Close-up view — 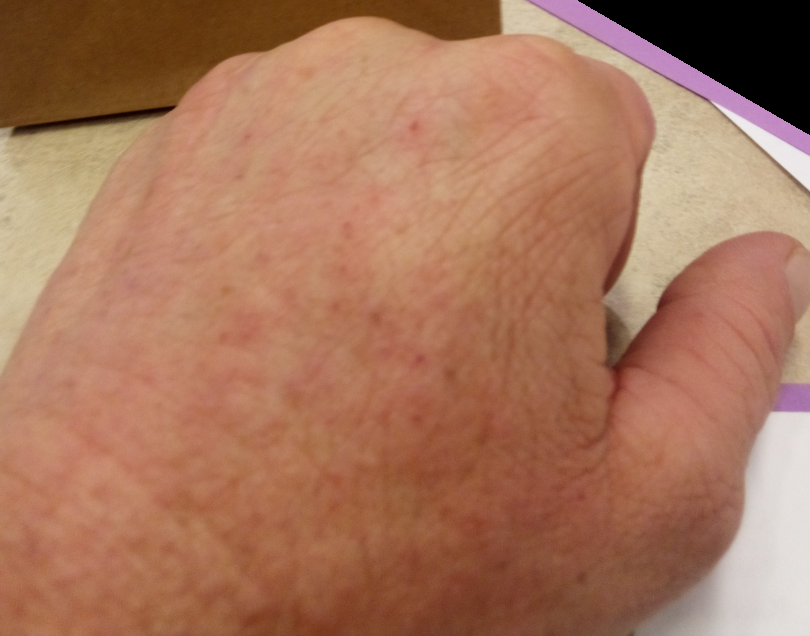<summary>
<assessment>not assessable</assessment>
</summary>